A dermoscopic photograph of a skin lesion.
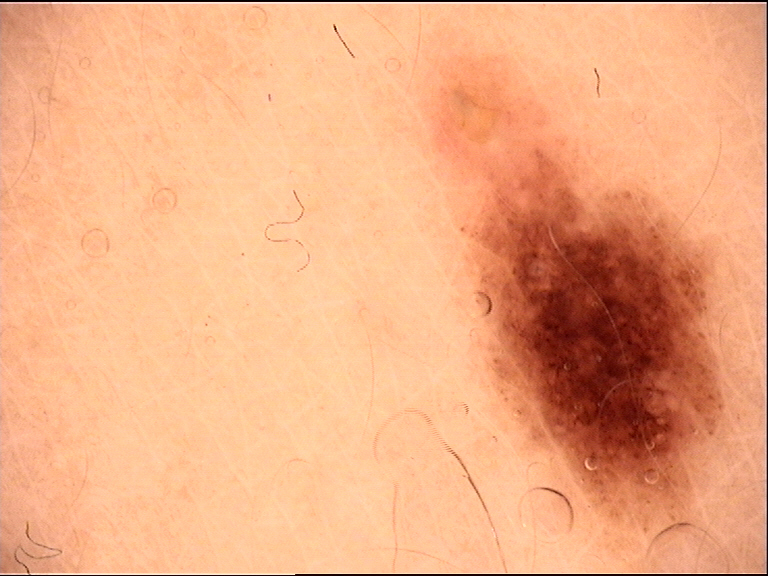Consistent with a dysplastic junctional nevus.